A female subject aged 38.
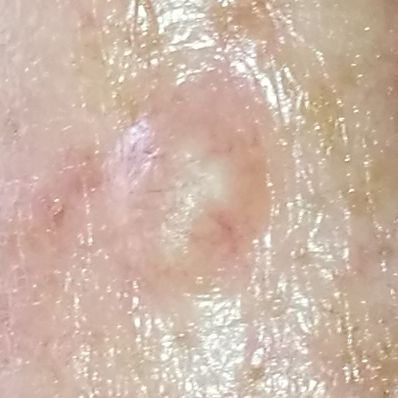Q: Any reported symptoms?
A: elevation / no itching, no pain
Q: What is the diagnosis?
A: basal cell carcinoma (biopsy-proven)